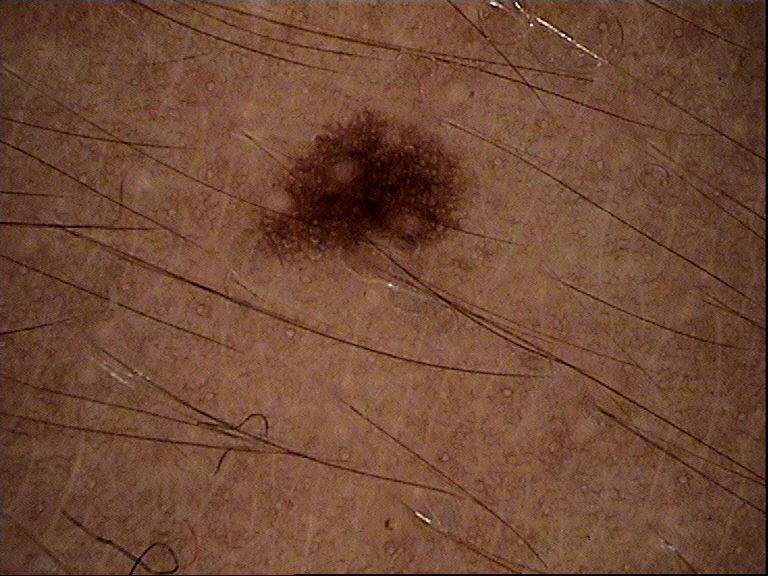Dermoscopy of a skin lesion.
Labeled as a dysplastic junctional nevus.